A contact-polarized dermoscopy image of a skin lesion. A male patient aged approximately 70. The patient is Fitzpatrick skin type II — 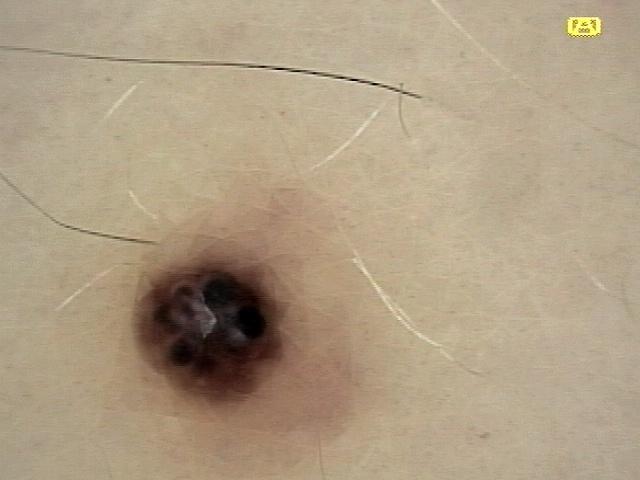site: the anterior trunk
assessment: vascular lesion